The back of the hand, arm and leg are involved · this is a close-up image · the patient is female:
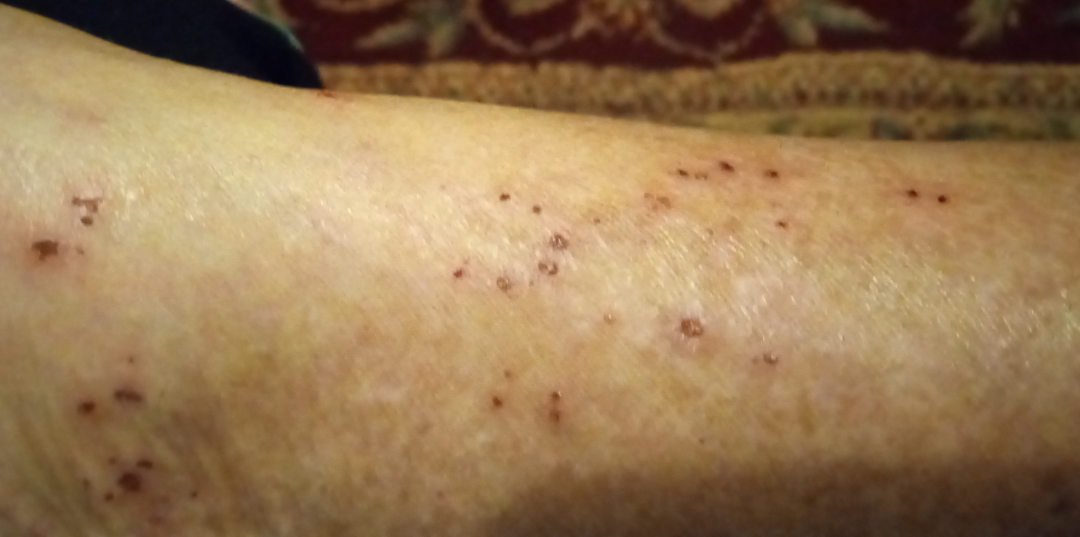{"duration": "more than one year", "texture": "raised or bumpy", "symptoms": "itching", "differential": "Eczema"}